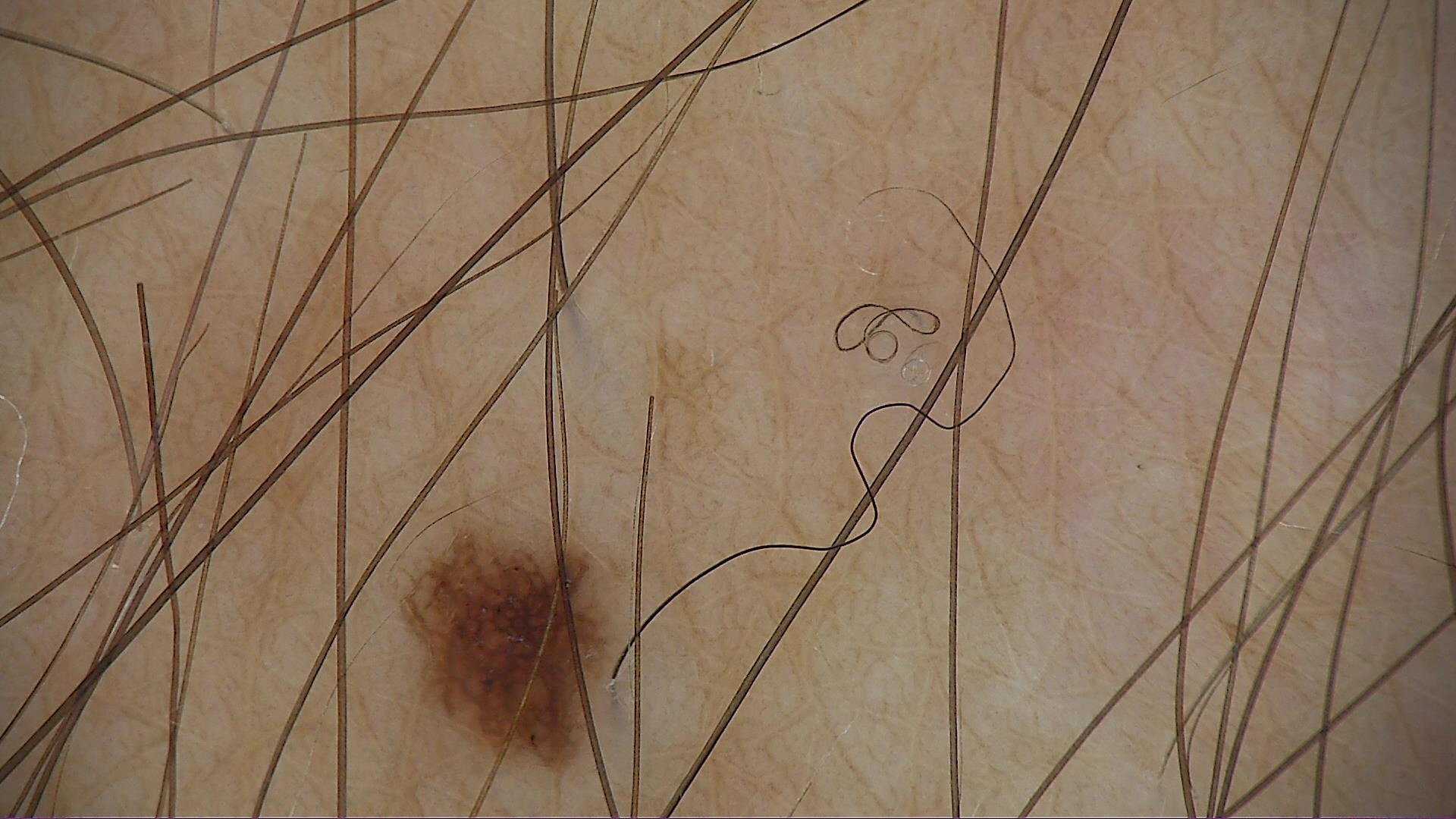Impression:
The diagnostic label was a junctional nevus.